Recorded as FST II; an overview clinical photograph of a skin lesion; a female patient aged around 85 or older: 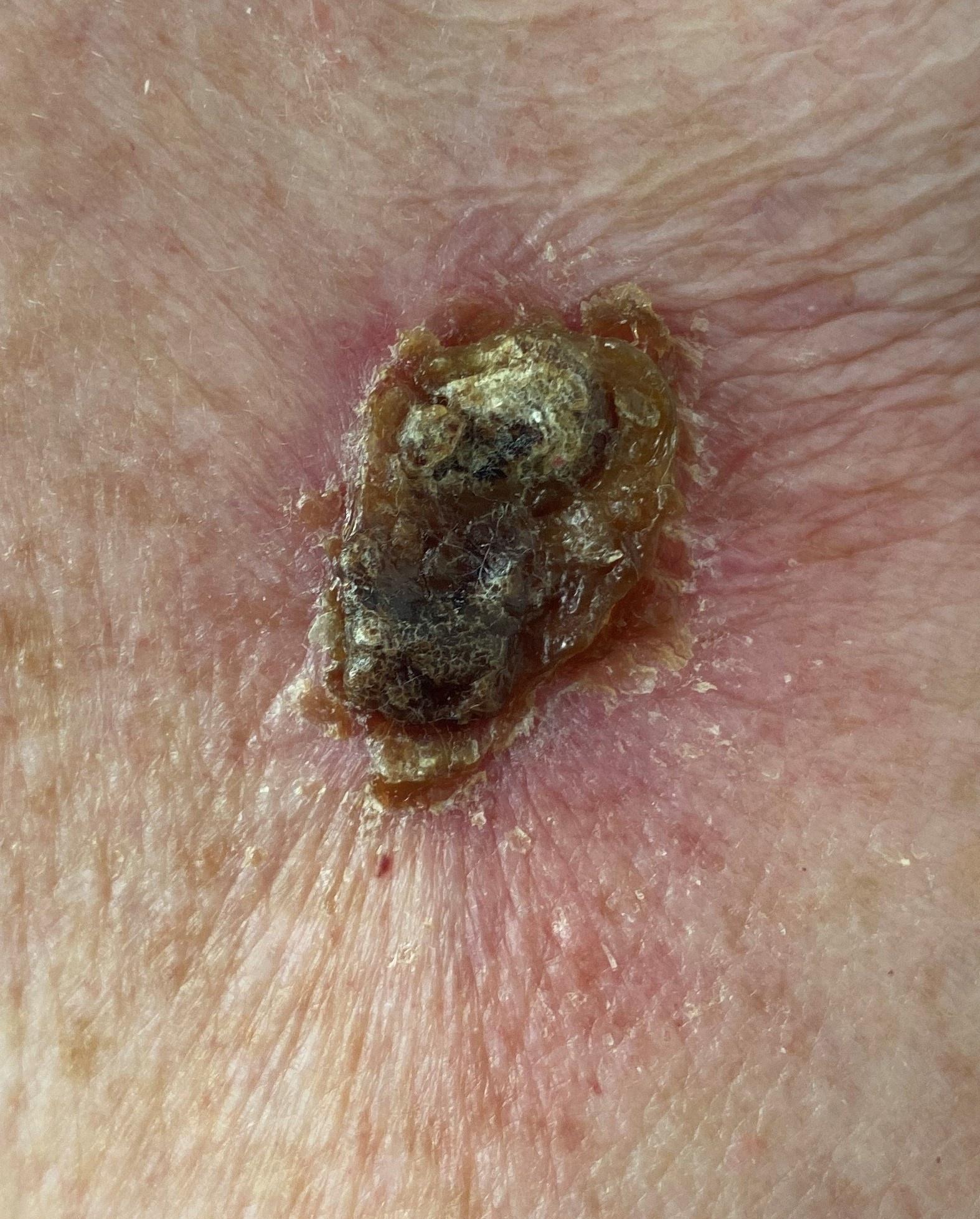Clinical context: The lesion was found on an upper extremity. Pathology: The biopsy diagnosis was a basal cell carcinoma.